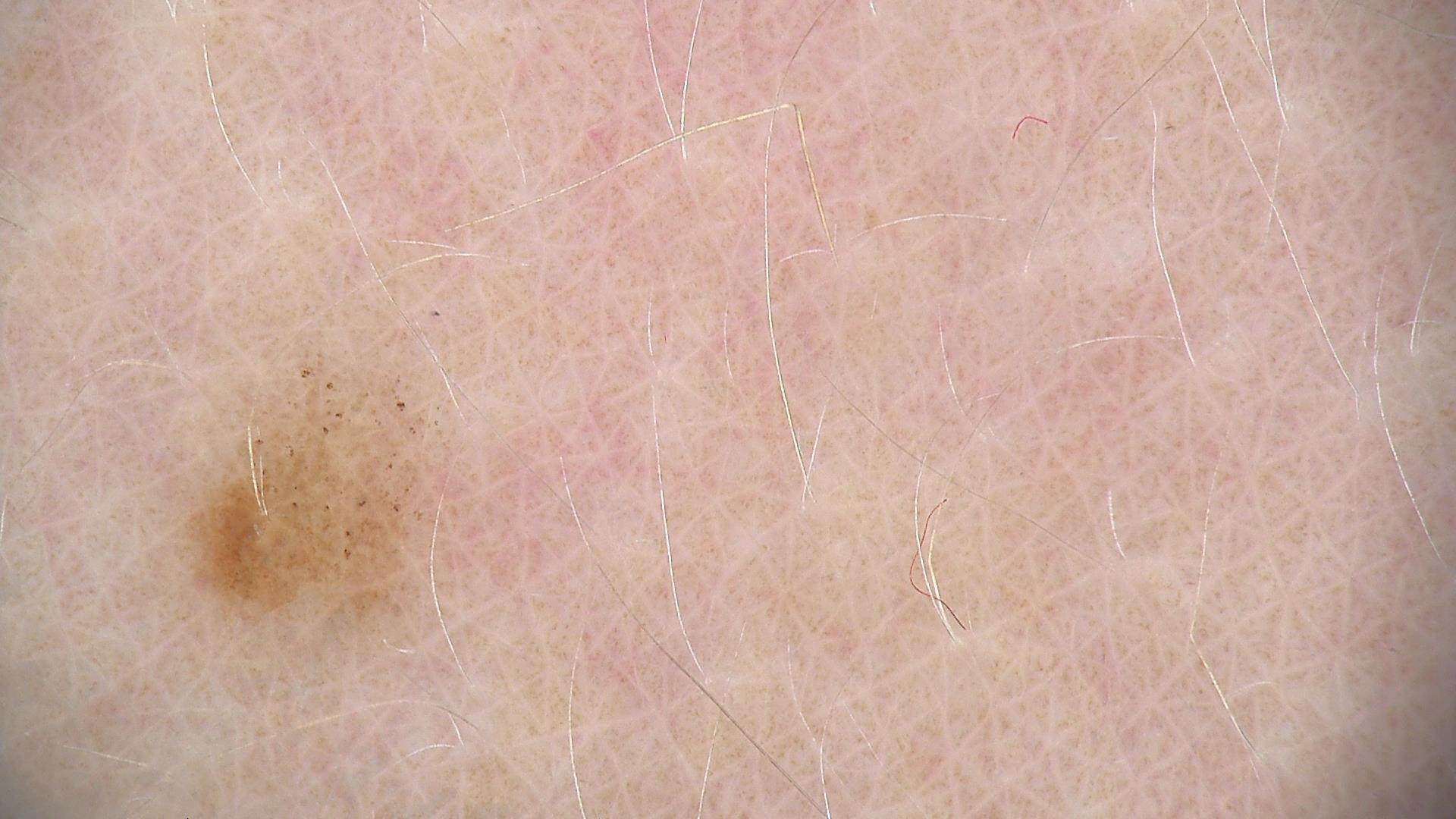Findings:
• image — dermoscopy
• class — dysplastic junctional nevus (expert consensus)